The arm and leg are involved; the patient is 30–39, female; an image taken at an angle:
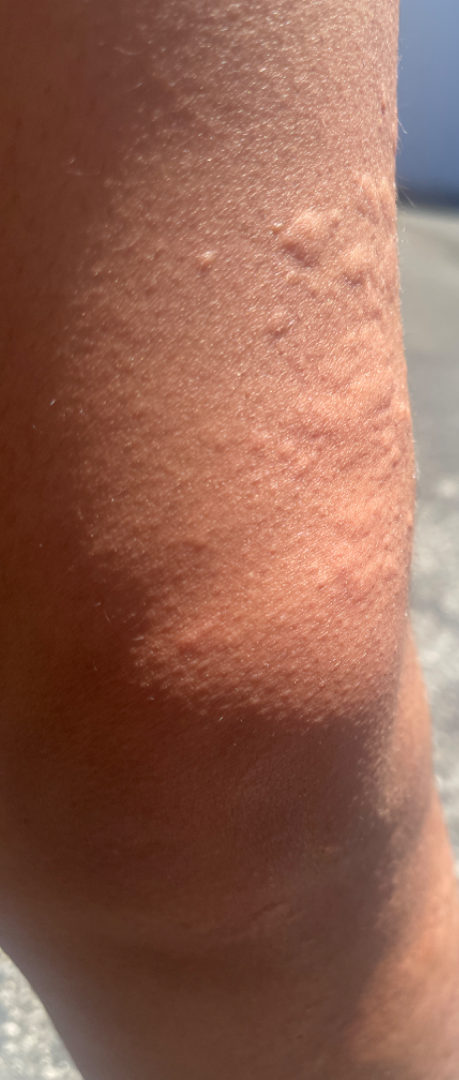Notes:
- clinical impression: Urticaria (primary)